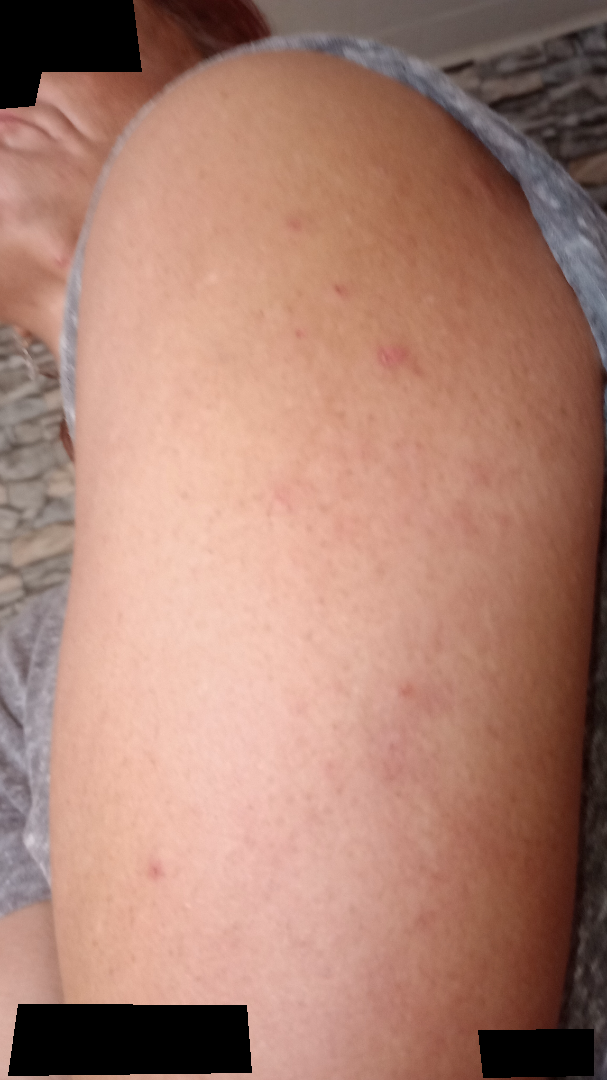Impression: The case was difficult to assess from the available photograph. History: The photo was captured at a distance. The patient is a female aged 40–49. The affected area is the back of the torso, leg and arm.